A skin lesion imaged with a dermatoscope. A female subject, in their mid- to late 30s — 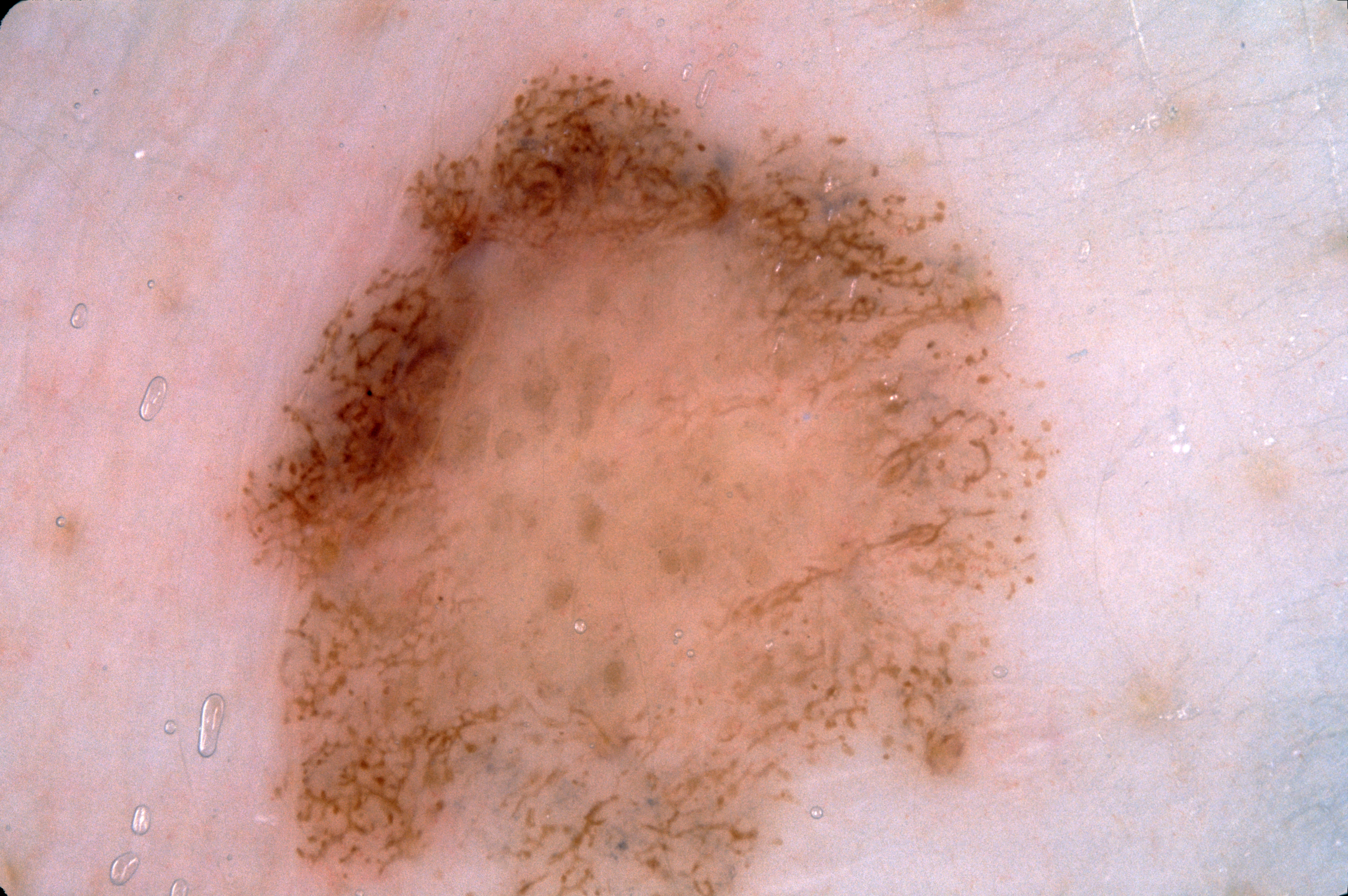features = pigment network
lesion size = large
location = (193, 0, 1054, 895)
lesion margin = clipped at the frame edge
assessment = a melanocytic nevus, a benign skin lesion